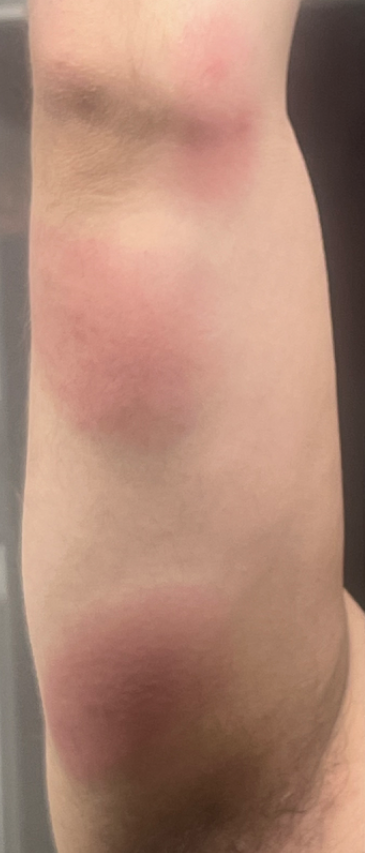{
  "differential": {
    "leading": [
      "Insect Bite"
    ],
    "considered": [
      "Urticaria"
    ],
    "unlikely": [
      "Panniculitis"
    ]
  }
}